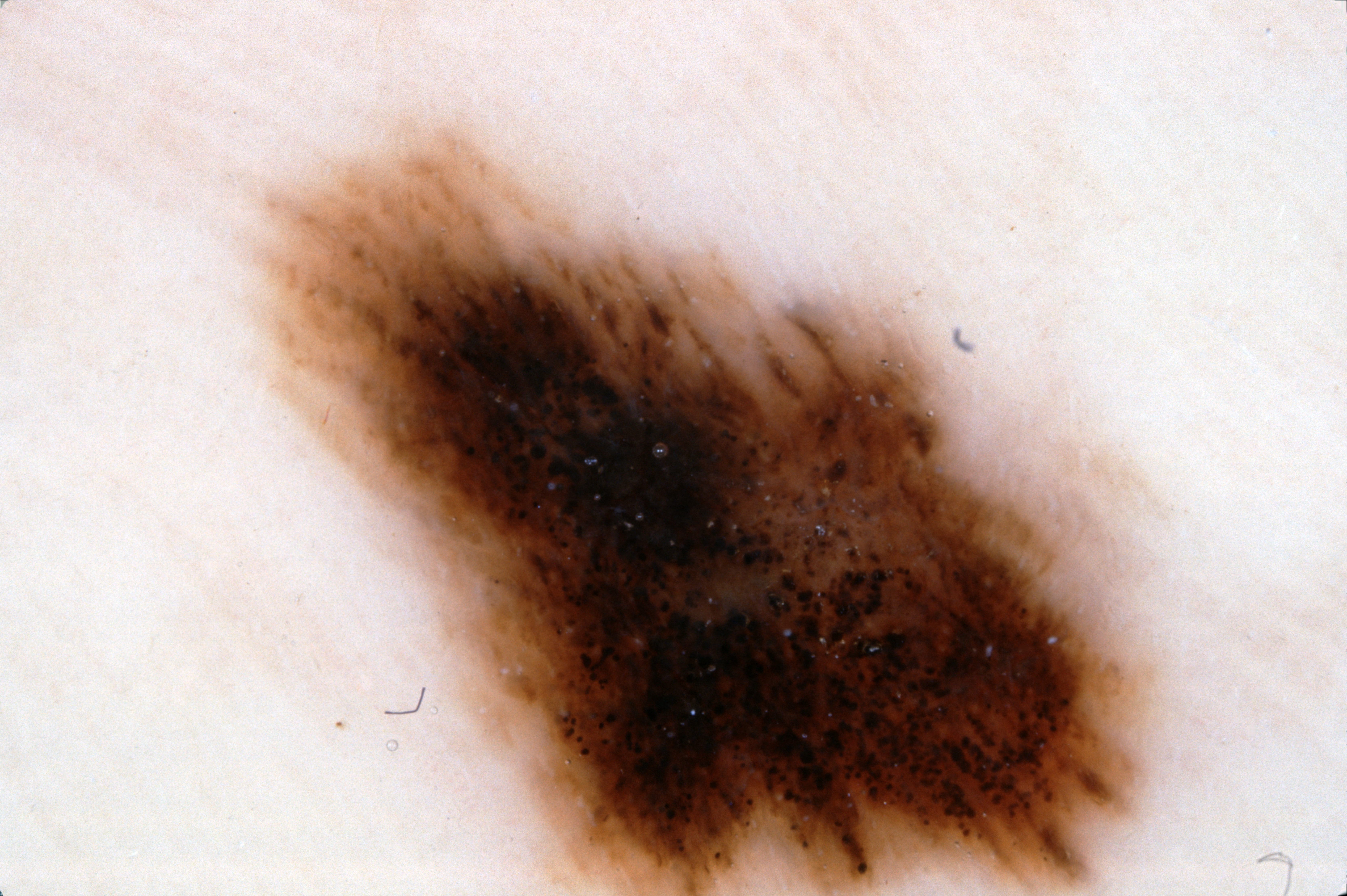image type = dermoscopy | lesion margin = extends past the field edge | dermoscopic features assessed but absent = pigment network, negative network, streaks, and milia-like cysts | lesion location = <bbox>268, 138, 1153, 895</bbox> | size = ~34% of the field | impression = a melanoma, a malignant lesion.